A dermatoscopic image of a skin lesion.
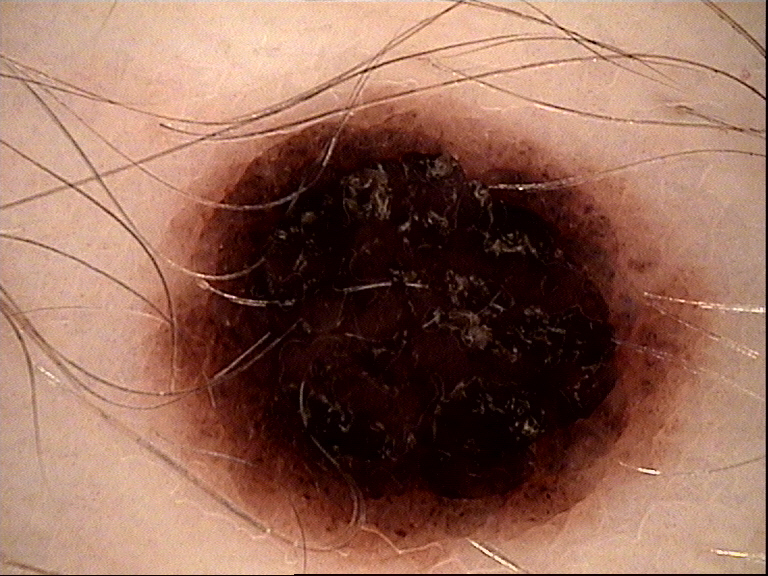This is a banal lesion.
The diagnostic label was a compound nevus.